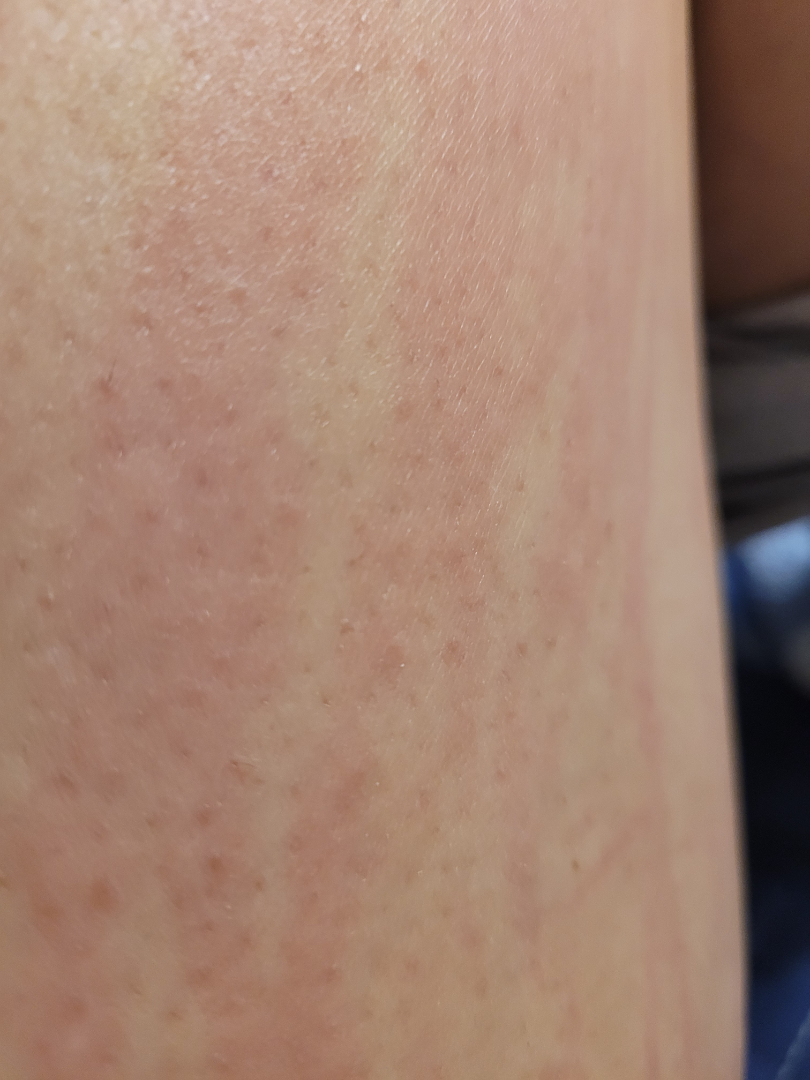Findings:
* photo taken · at an angle
* dermatologist impression · consistent with Urticaria